Located on the leg. Close-up view. The patient indicates the lesion is raised or bumpy. No constitutional symptoms were reported. Present for one to four weeks. Reported lesion symptoms include itching. The patient described the issue as a rash. Male patient, age 18–29: 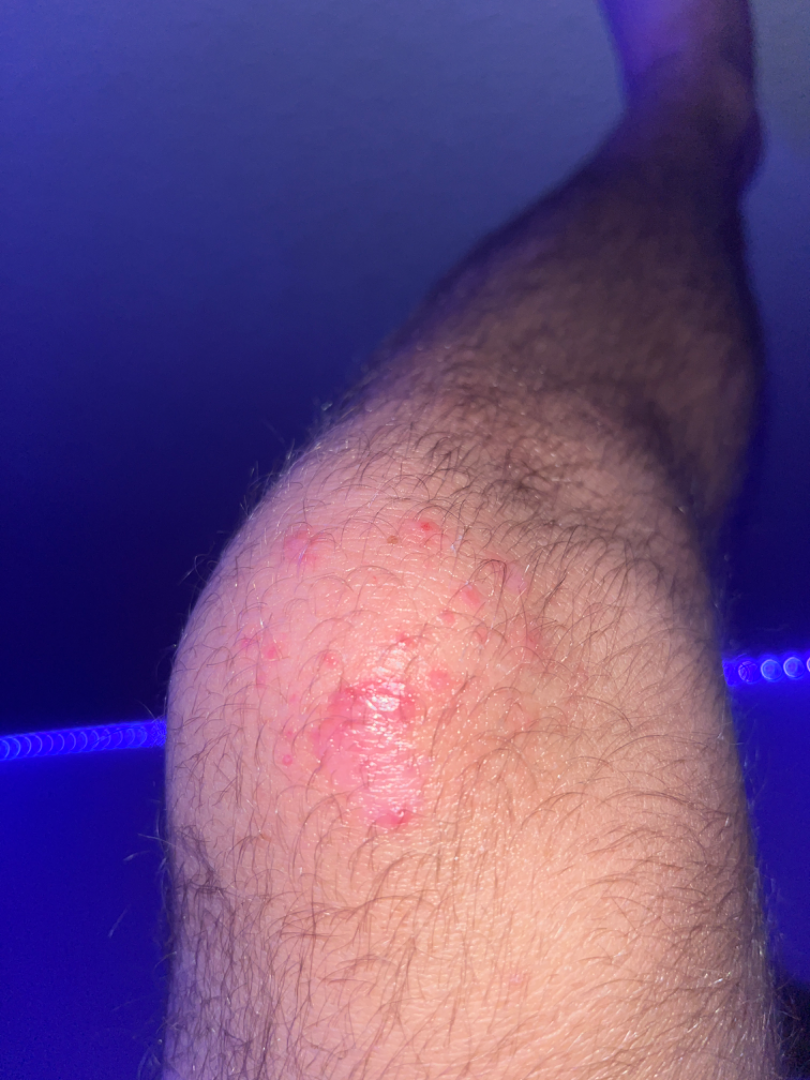The image was not sufficient for the reviewer to characterize the skin condition.